The lesion involves the top or side of the foot and leg. A close-up photograph. Non-clinician graders estimated Monk skin tone scale 1 (US pool) or 3 (India pool). The patient is 30–39, male. Symptoms reported: pain, itching, bothersome appearance and burning: 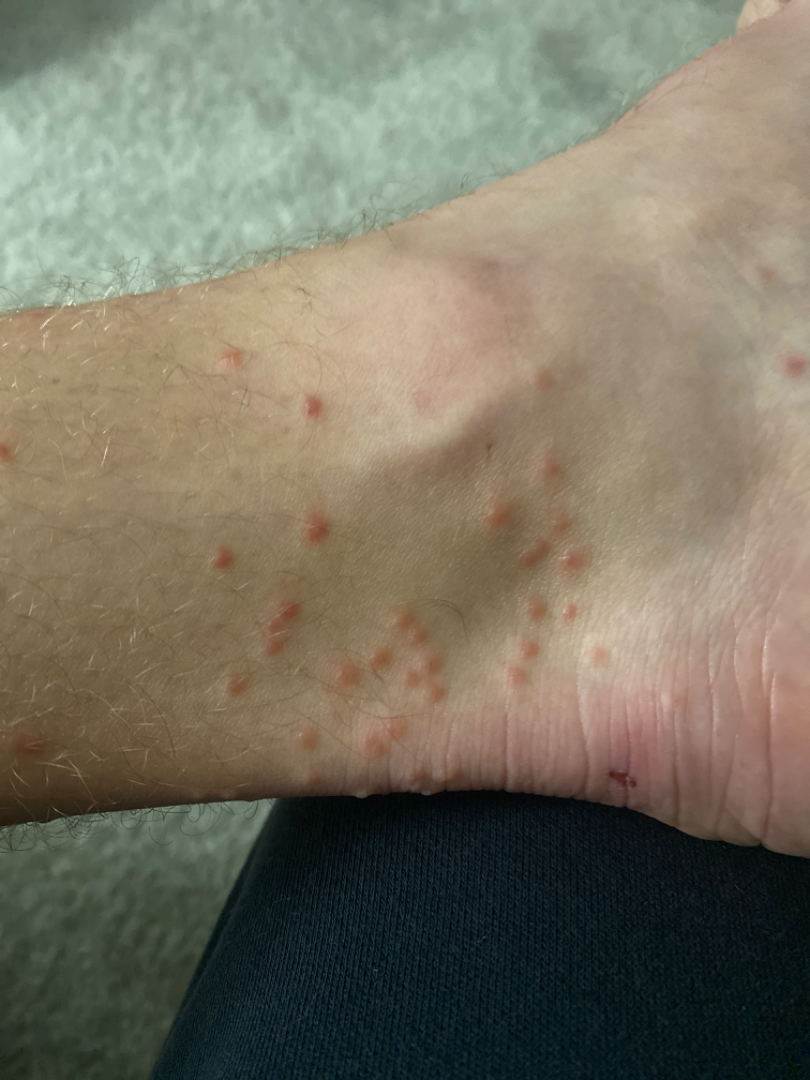dermatologist impression = Lichen planus/lichenoid eruption and Insect Bite were each considered, in no particular order; less probable is Eczema